The patient described the issue as a rash. Skin tone: Fitzpatrick skin type V; lay reviewers estimated MST 3 or 6. Located on the arm. Present for one to four weeks. This is a close-up image:
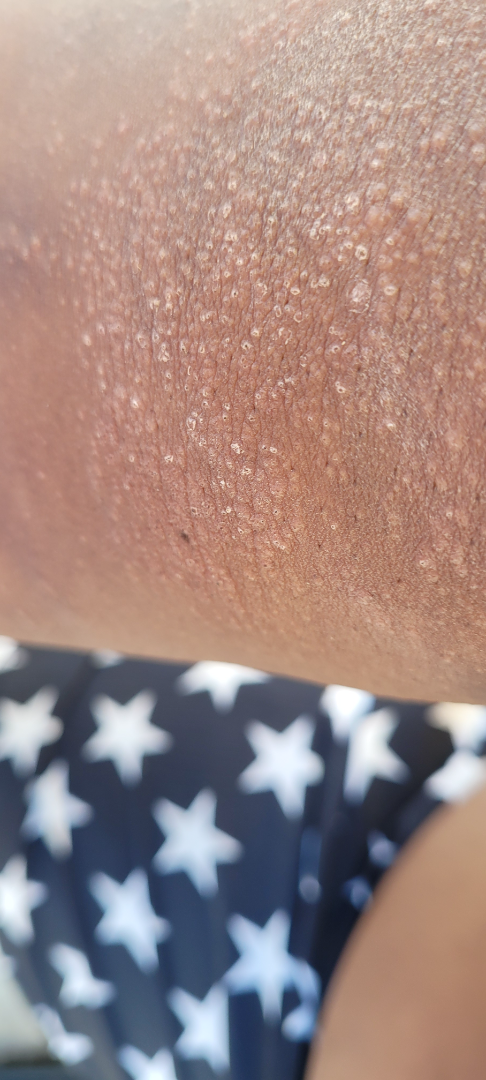Notes:
• differential · Chronic dermatitis, NOS (considered); Eczema (considered); Photodermatitis (lower probability); Sunburn (lower probability); Lichen nitidus (lower probability); Lichen Simplex Chronicus (lower probability); Allergic Contact Dermatitis (lower probability)